The lesion involves the arm, head or neck, front of the torso, back of the torso and leg · the photo was captured at an angle: 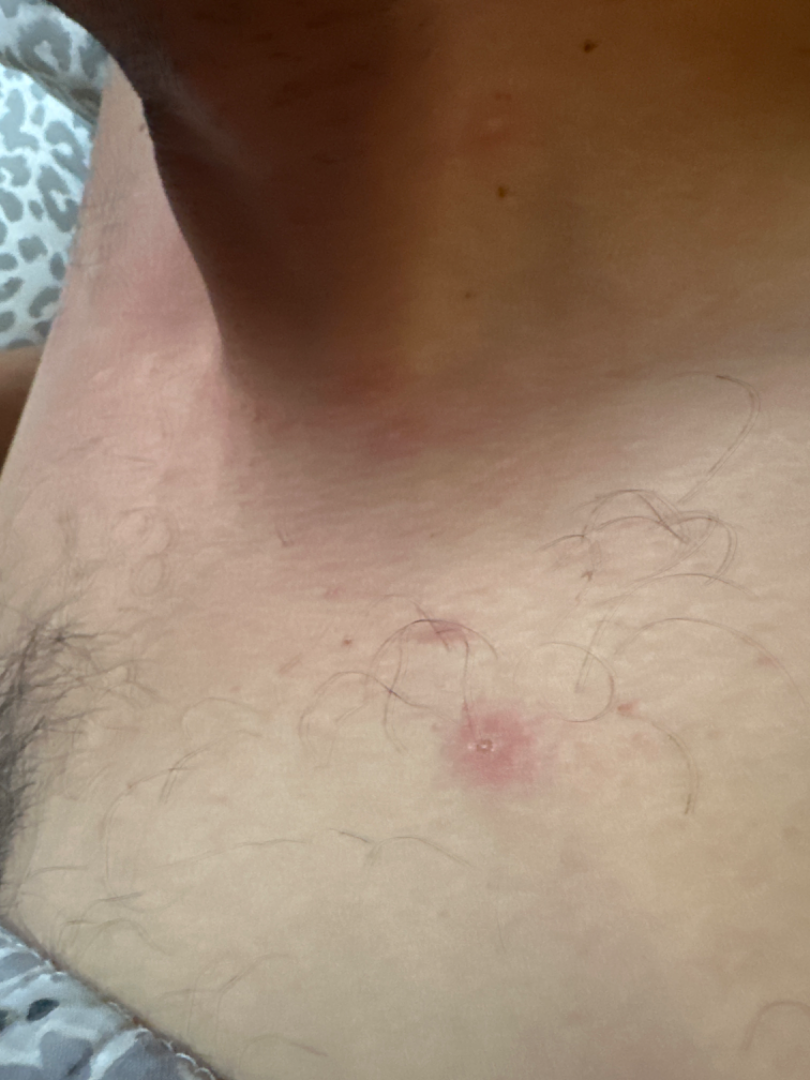Notes:
• clinical impression: Scar Condition (leading); Folliculitis (possible); Acne (possible)